A dermoscopic close-up of a skin lesion.
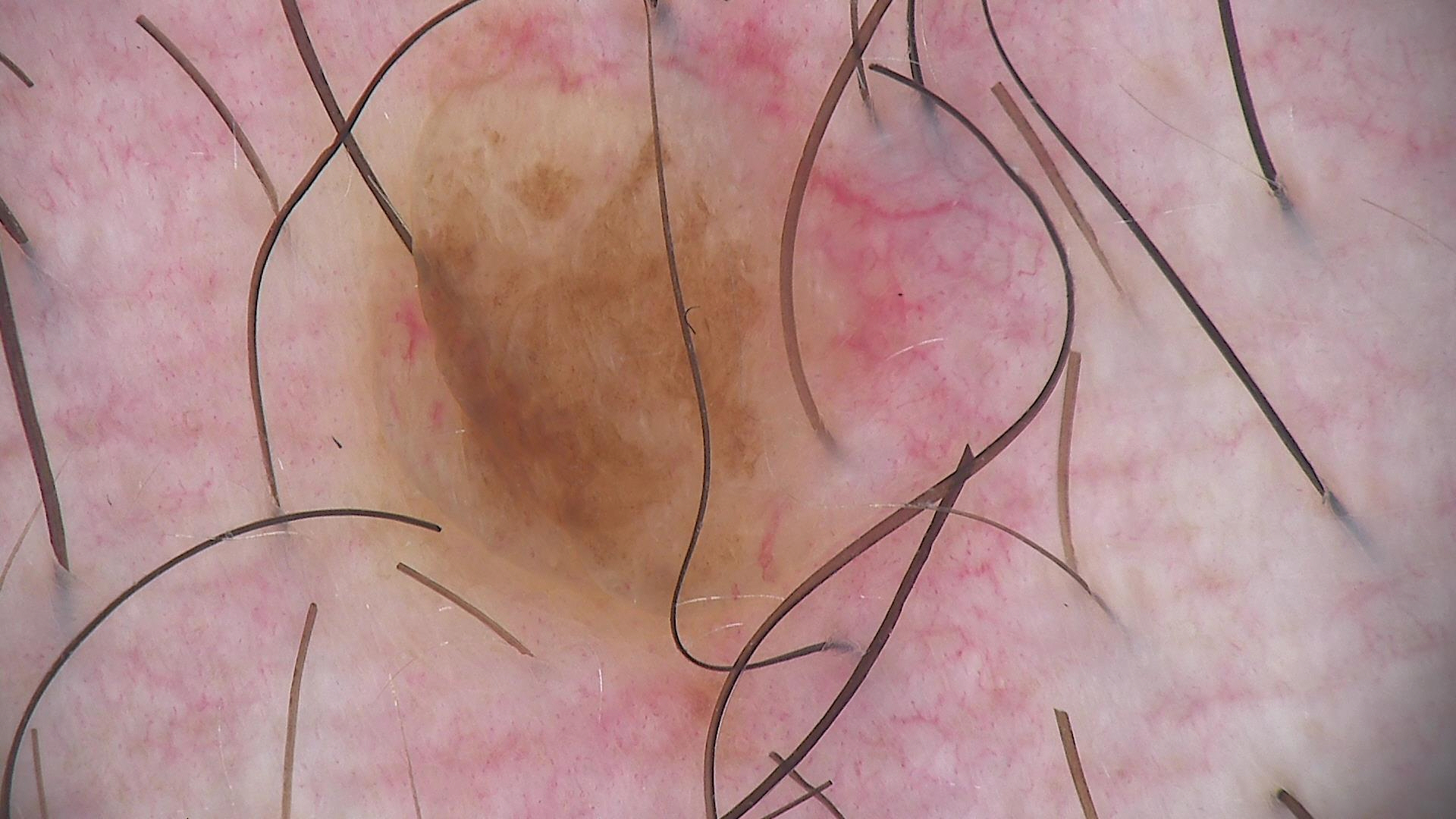{
  "lesion_type": {
    "main_class": "banal",
    "pattern": "dermal"
  },
  "diagnosis": {
    "name": "dermal nevus",
    "code": "db",
    "malignancy": "benign",
    "super_class": "melanocytic",
    "confirmation": "expert consensus"
  }
}